The contributor is female. The back of the torso is involved. A close-up photograph:
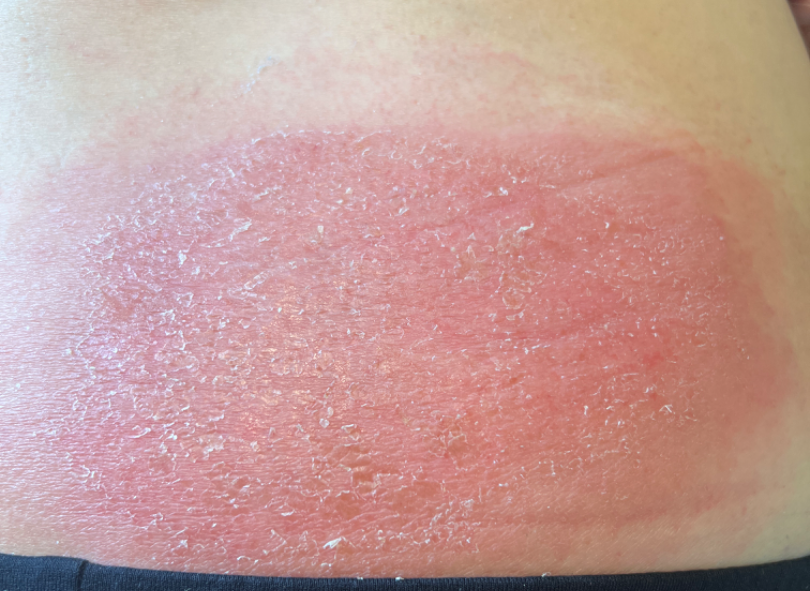other reported symptoms: chills
symptoms: pain, enlargement, burning and itching
patient's own categorization: a rash
present for: one to three months
surface texture: fluid-filled, raised or bumpy and rough or flaky
diagnostic considerations: the primary impression is Cellulitis